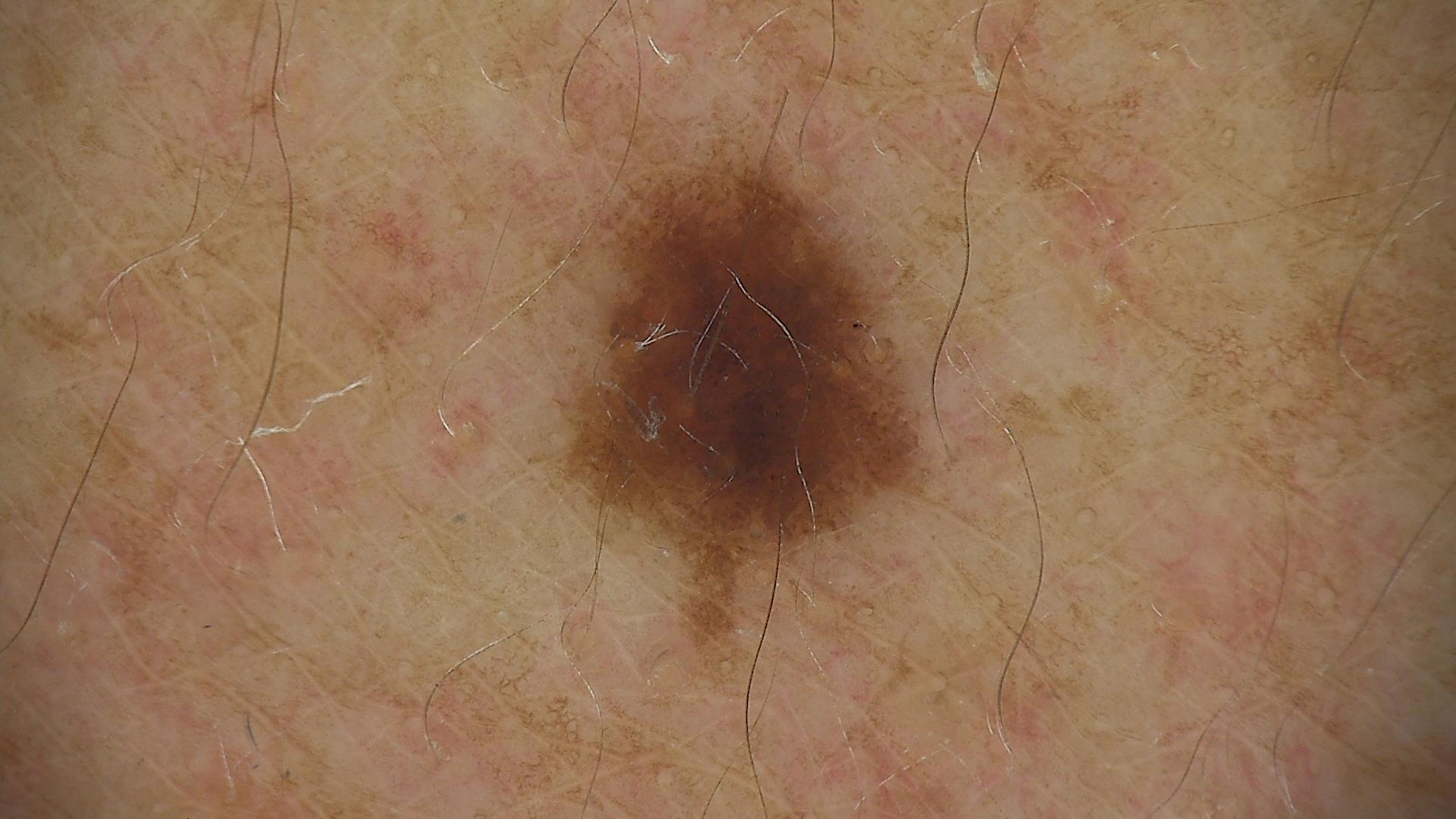Impression: Consistent with a dysplastic junctional nevus.